A patient 74 years old; a clinical photo of a skin lesion taken with a smartphone: 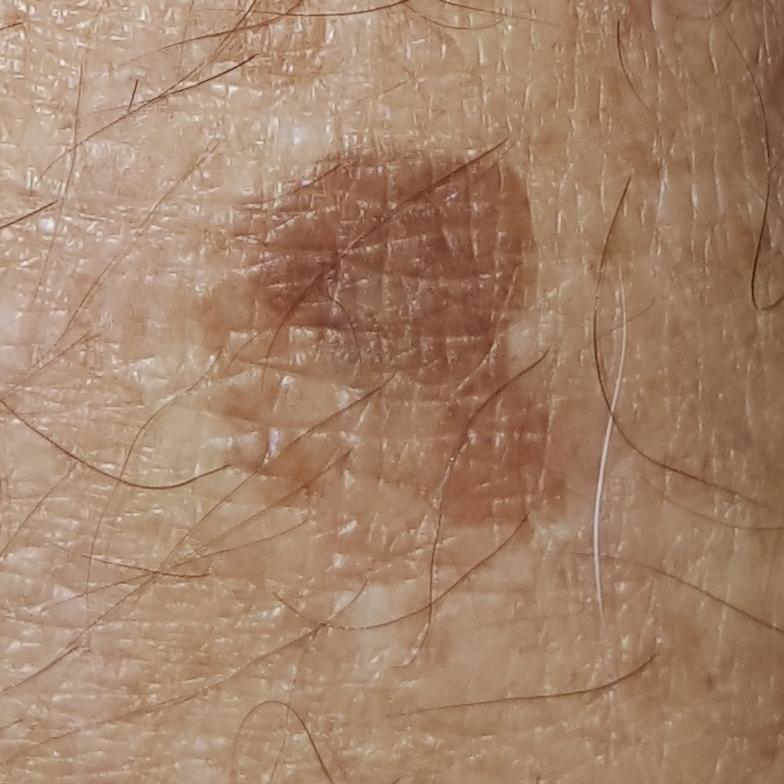Q: Where on the body is the lesion?
A: a forearm
Q: What was the clinical impression?
A: seborrheic keratosis (clinical consensus)